The lesion involves the leg; an image taken at a distance: 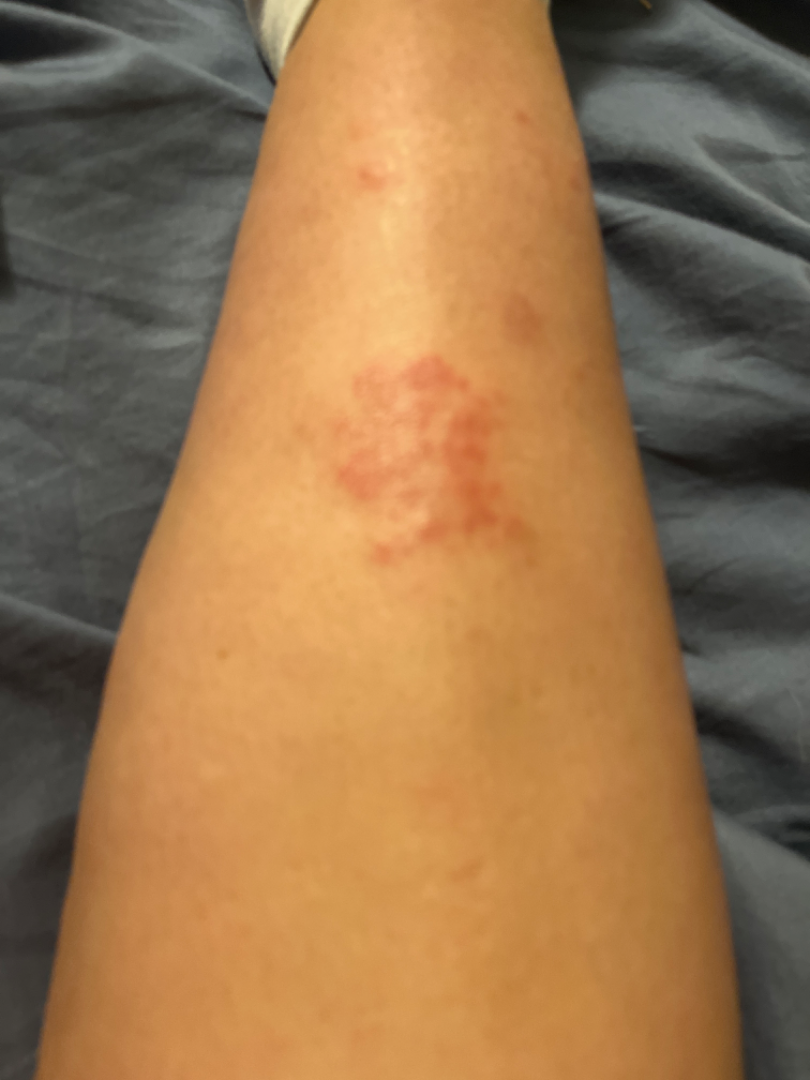Findings:
The image was not sufficient for the reviewer to characterize the skin condition.